Male contributor, age 50–59. The affected area is the arm. The photo was captured at an angle: 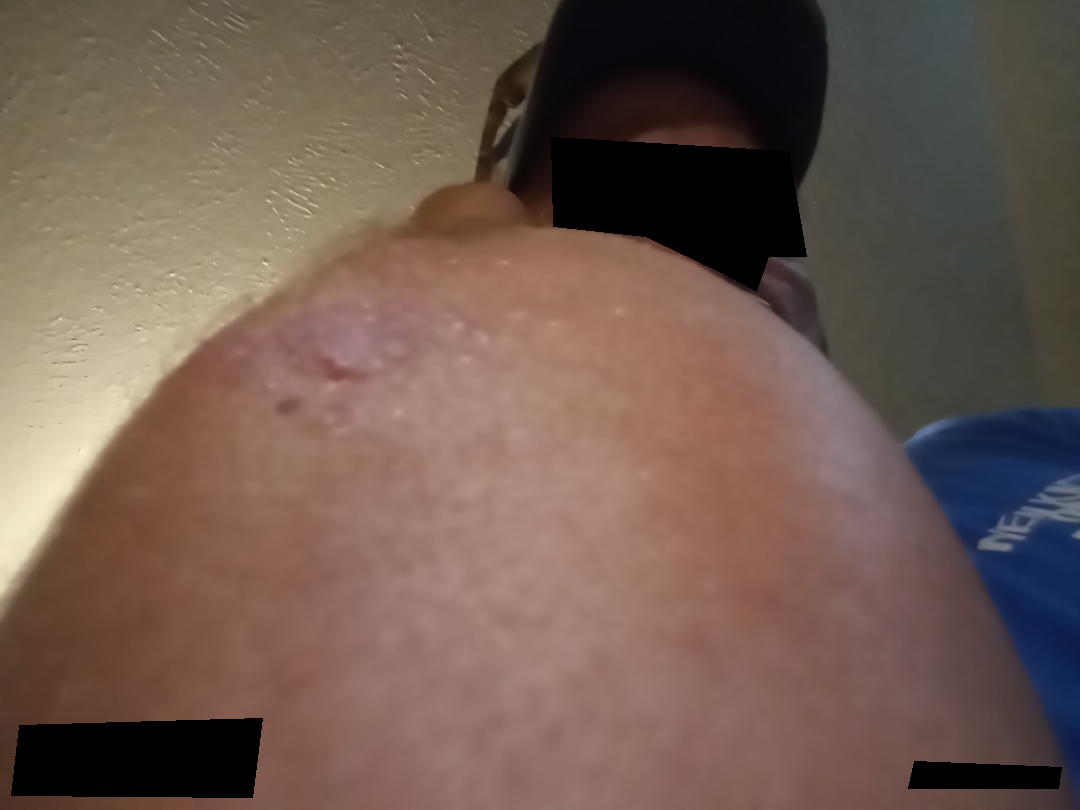The lesion is described as raised or bumpy.
Human graders estimated Monk Skin Tone 5 (US pool) or 3 (India pool).
The patient also reports fatigue and fever.
No associated lesion symptoms were reported.
On photographic review, the reviewer's impression was Contact dermatitis.